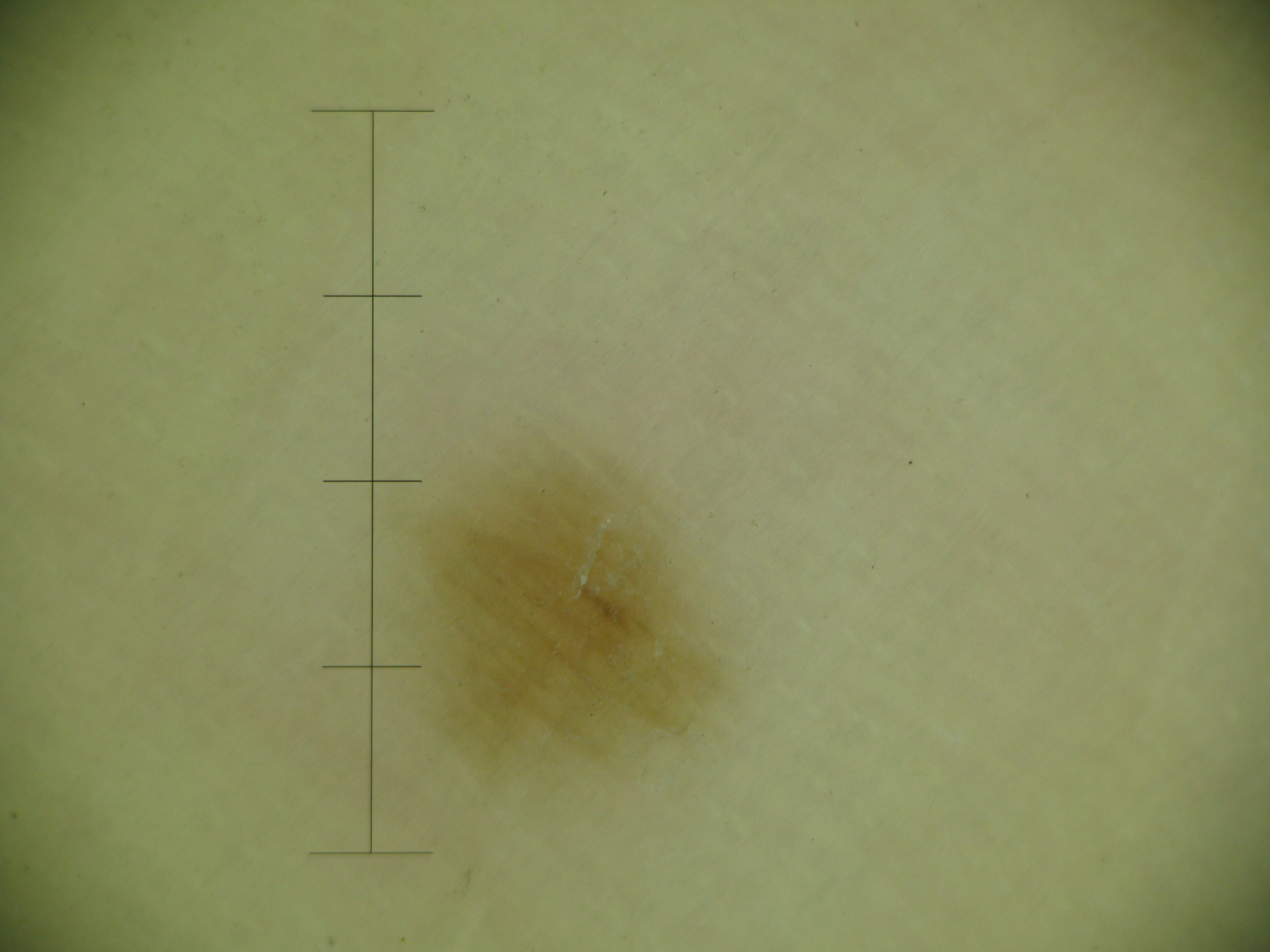diagnostic label: acral junctional nevus (expert consensus)